This is a close-up image, the arm and leg are involved:
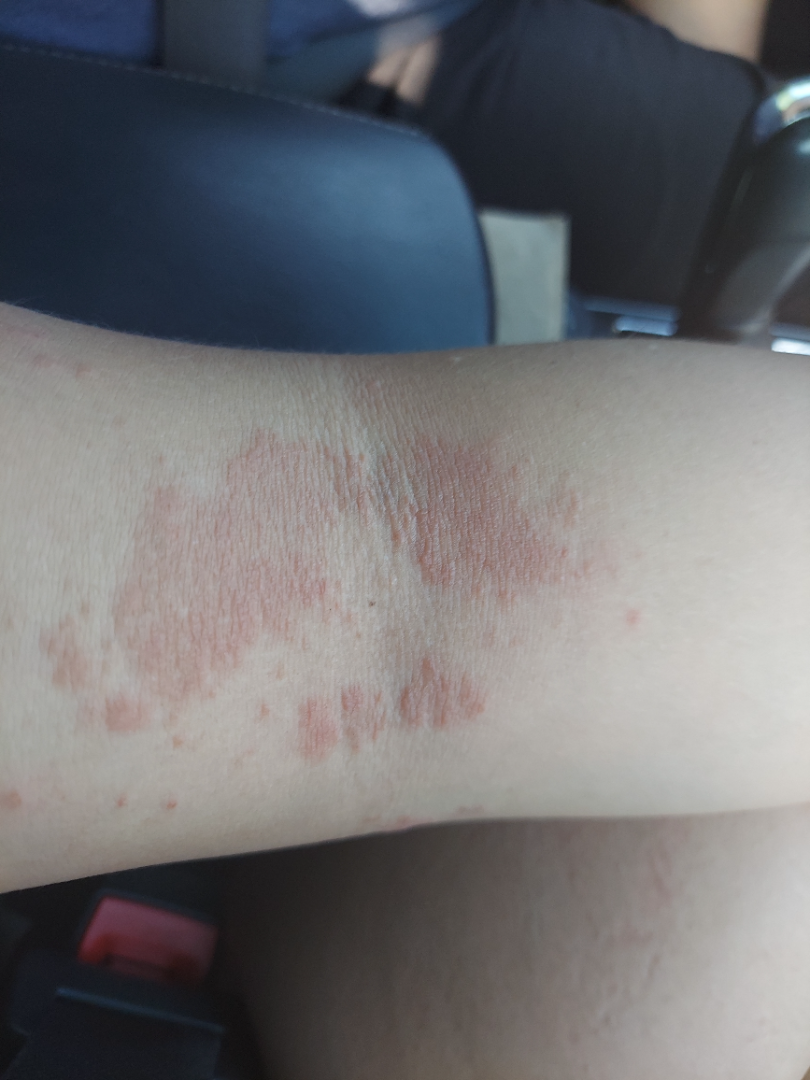Psoriasis (weight 0.50); Eczema (weight 0.50).